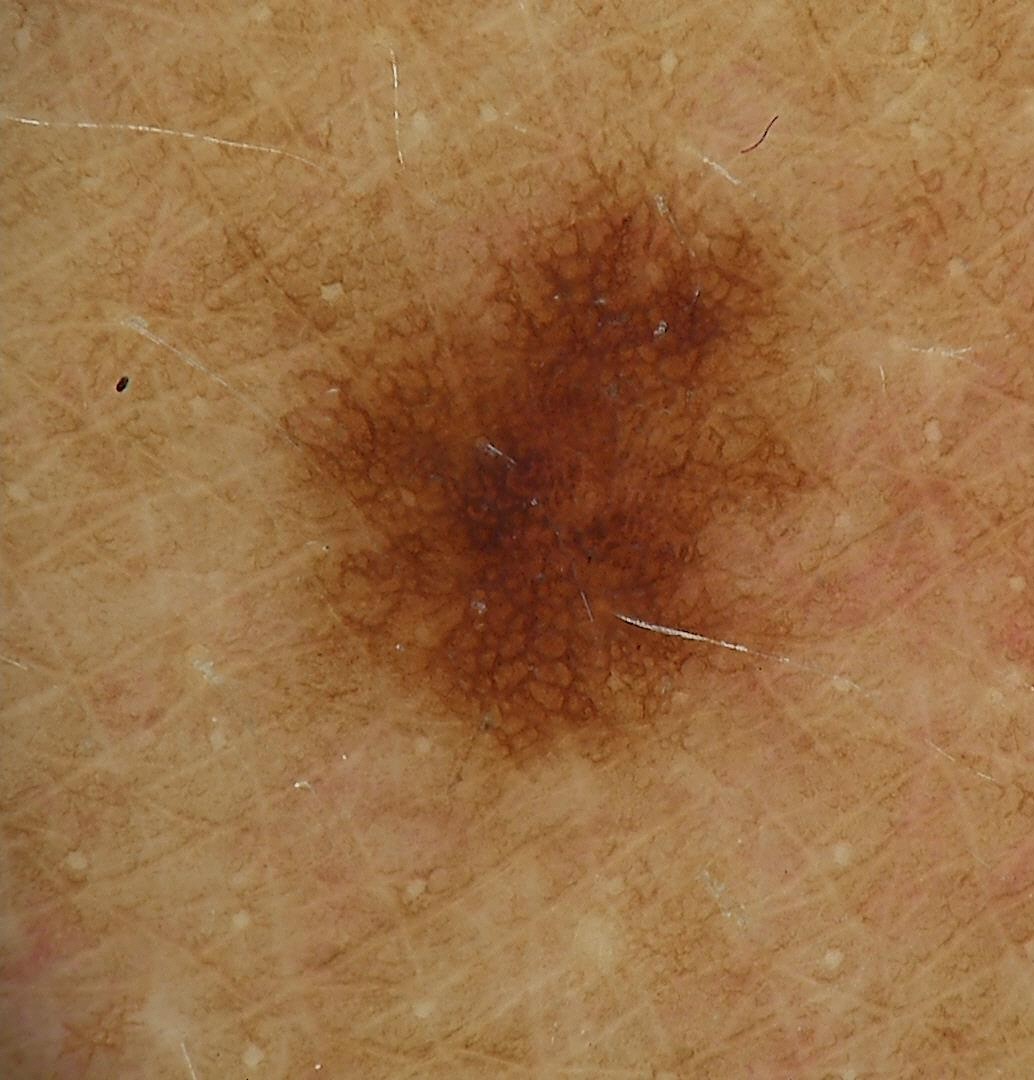<dermoscopy>
<image>dermoscopy</image>
<diagnosis>
<name>junctional nevus</name>
<code>jb</code>
<malignancy>benign</malignancy>
<super_class>melanocytic</super_class>
<confirmation>expert consensus</confirmation>
</diagnosis>
</dermoscopy>